A skin lesion imaged with a dermatoscope.
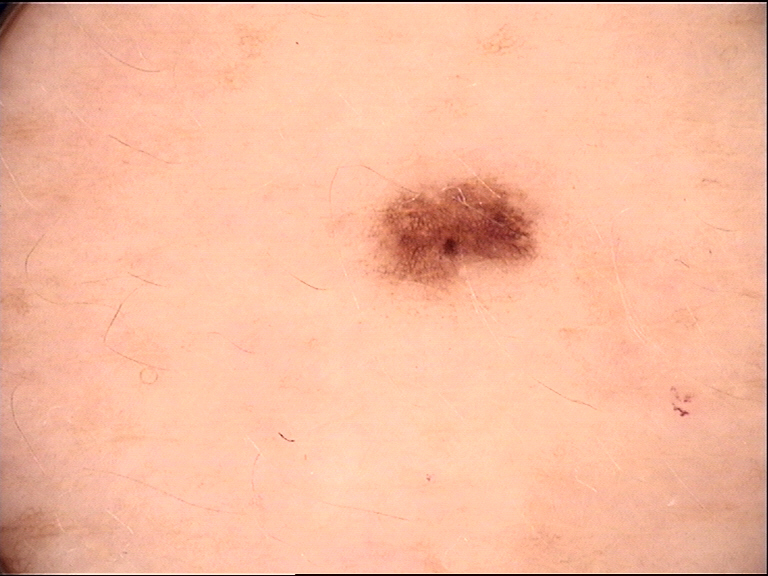Labeled as a dysplastic junctional nevus.